The lesion involves the leg and arm. The photograph is a close-up of the affected area. The patient is 40–49, female.
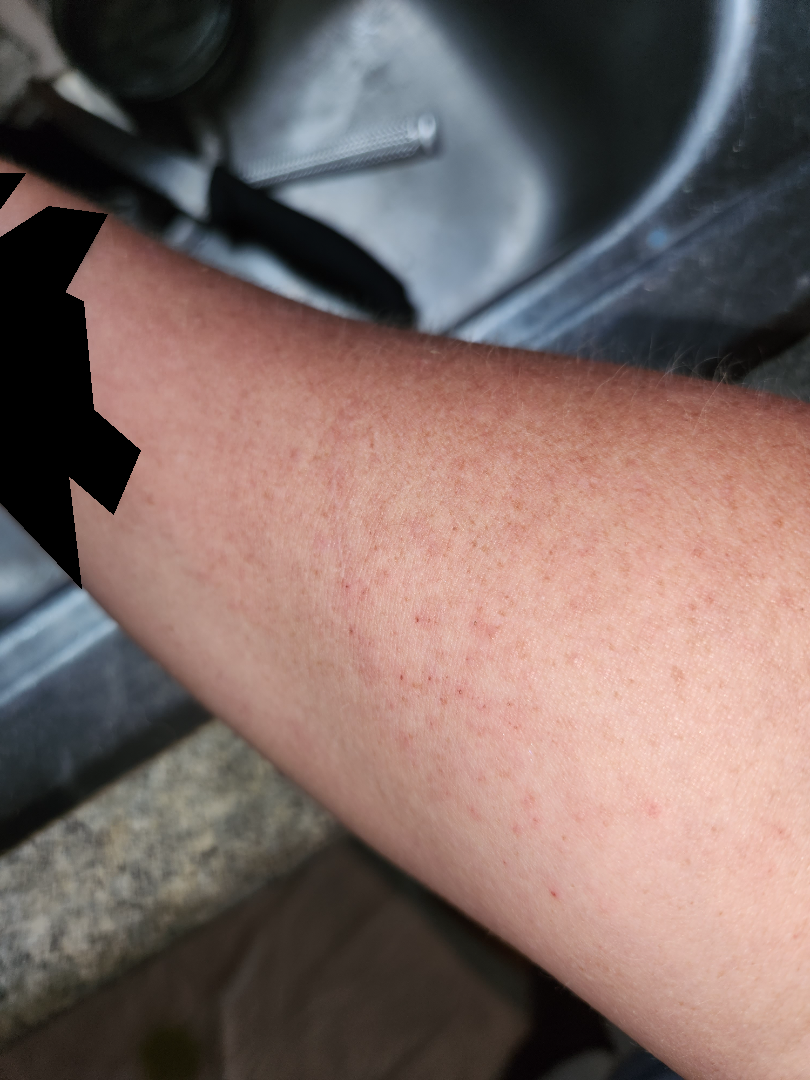The reviewing dermatologist was unable to assign a differential diagnosis from the image. The contributor reports the lesion is raised or bumpy. No associated systemic symptoms reported. The patient considered this a rash. Reported duration is one to four weeks. Symptoms reported: enlargement and itching.